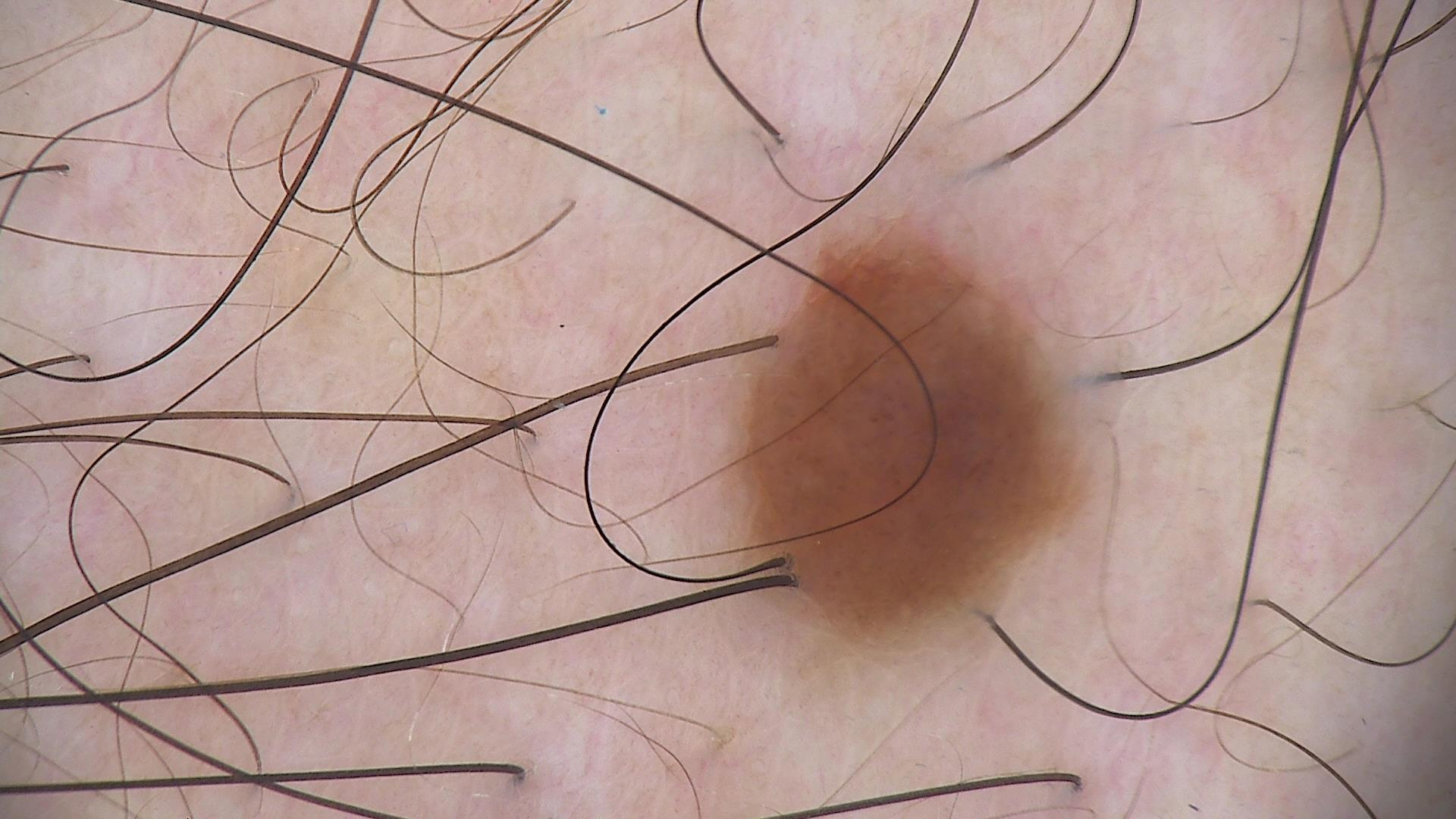Q: What is this lesion?
A: dysplastic junctional nevus (expert consensus)